The chart notes prior malignancy (patient or family) and pesticide exposure. The patient is Fitzpatrick II. A clinical photograph showing a skin lesion — 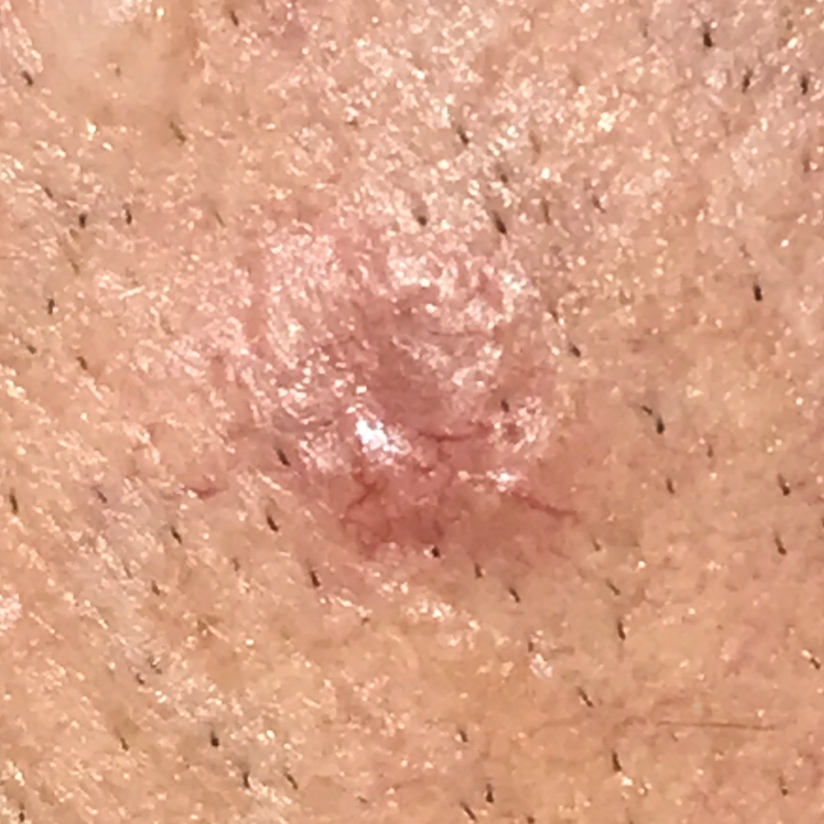{
  "lesion_size": {
    "diameter_1_mm": 10.0,
    "diameter_2_mm": 7.0
  },
  "symptoms": {
    "present": [
      "elevation",
      "itching"
    ]
  },
  "diagnosis": {
    "name": "basal cell carcinoma",
    "code": "BCC",
    "malignancy": "malignant",
    "confirmation": "histopathology"
  }
}